A skin lesion imaged with a dermatoscope:
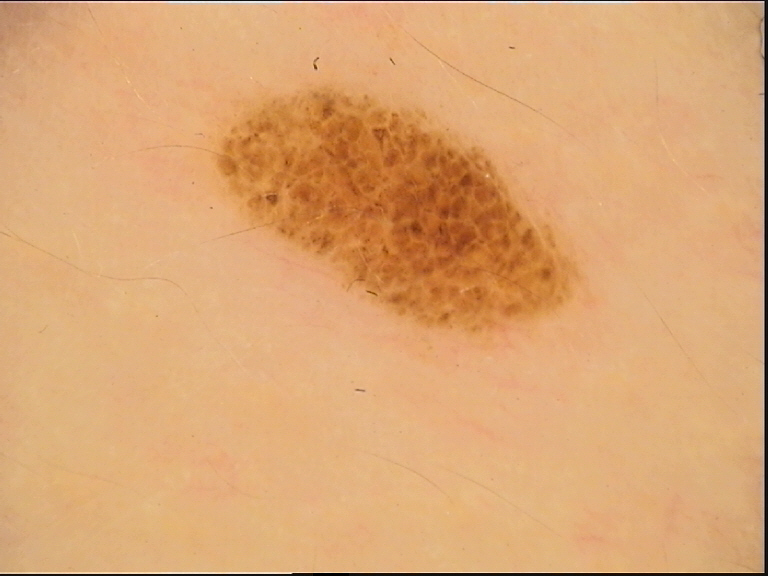| feature | finding |
|---|---|
| assessment | dysplastic compound nevus (expert consensus) |